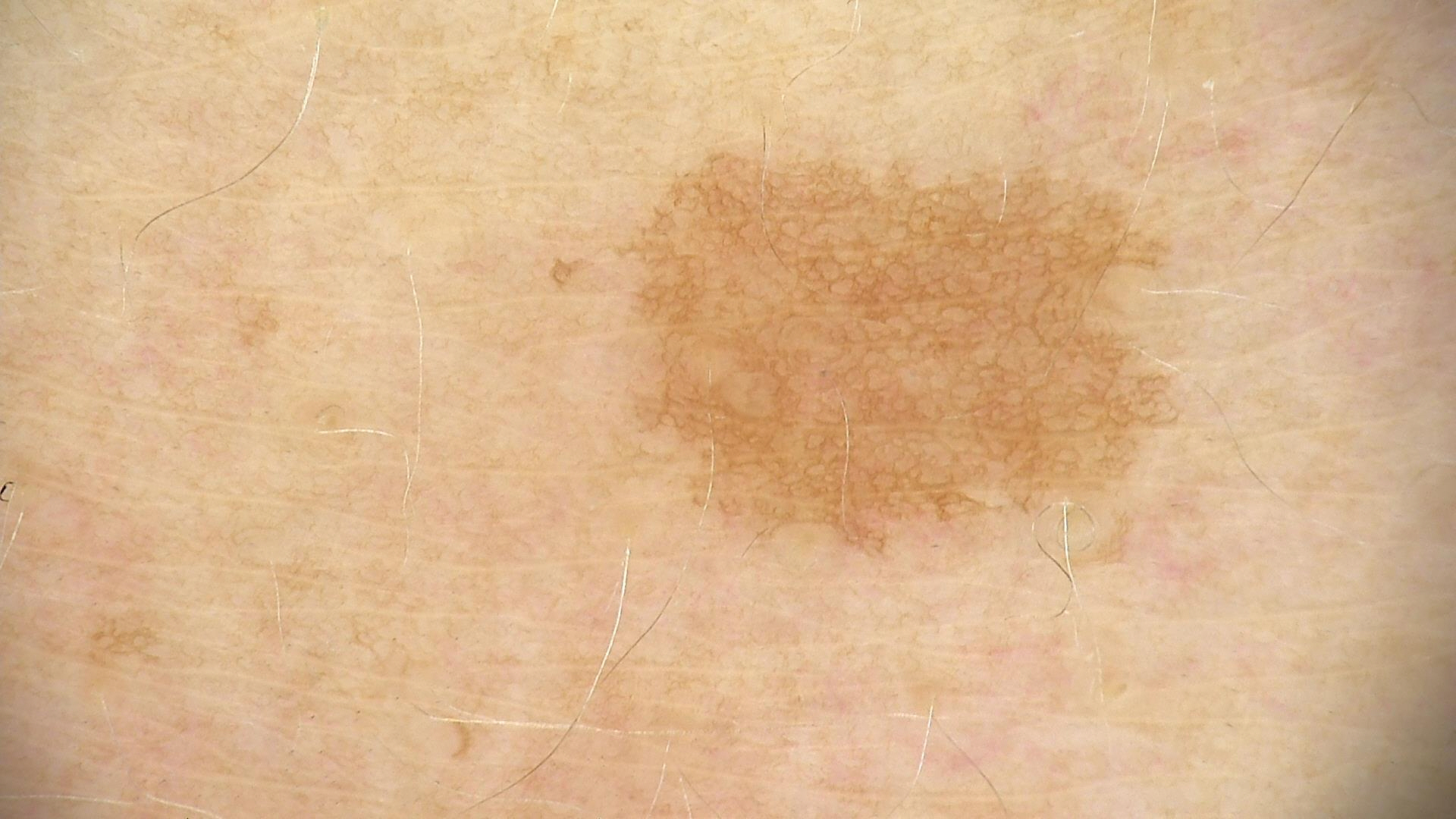A dermoscopic photograph of a skin lesion.
Labeled as a solar lentigo.